A male patient in their 60s · a clinical photo of a skin lesion taken with a smartphone · by history, tobacco use and no prior skin cancer (patient or family): 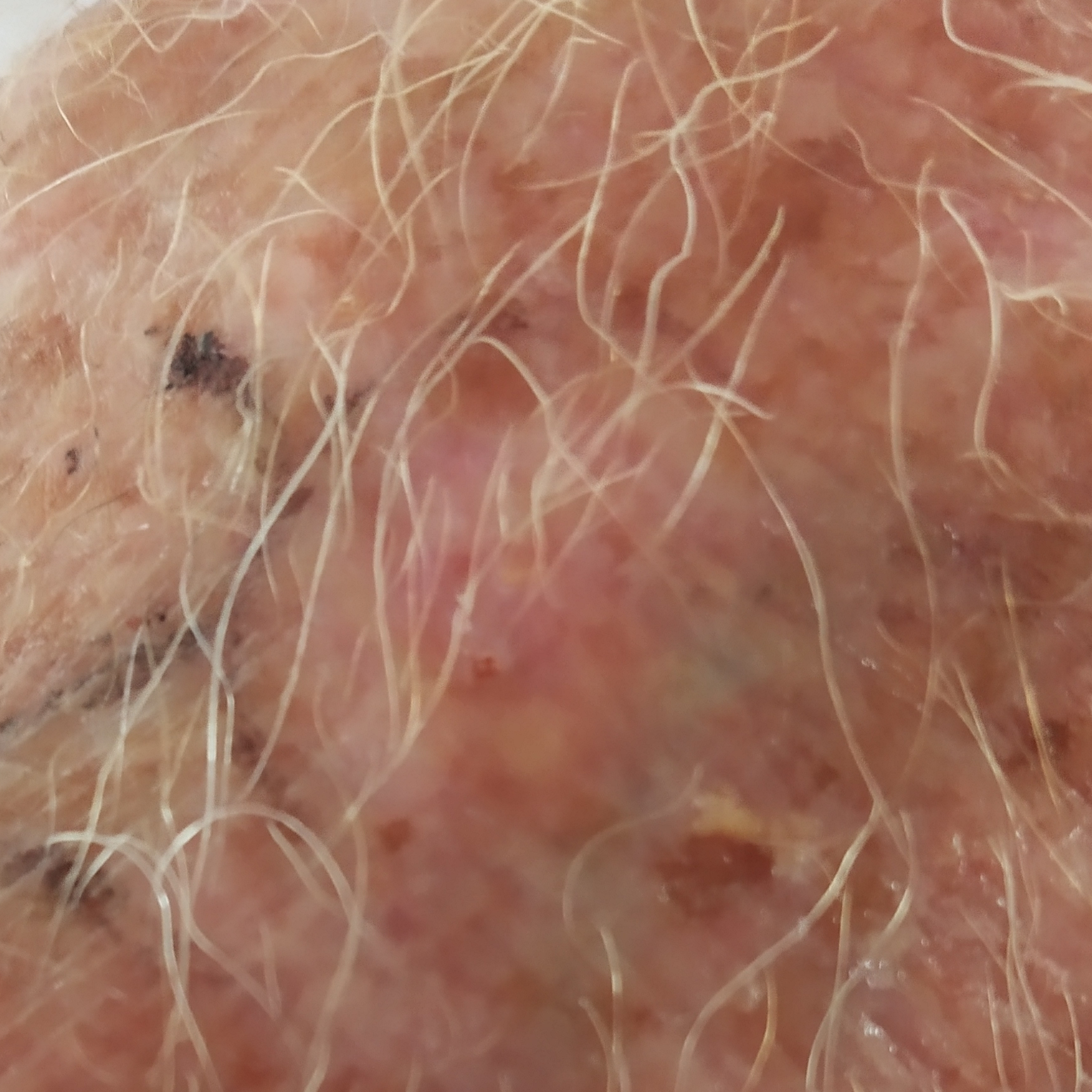Findings:
* anatomic site: a hand
* lesion size: approx. 20 × 15 mm
* symptoms: elevation, itching
* diagnosis: basal cell carcinoma (biopsy-proven)